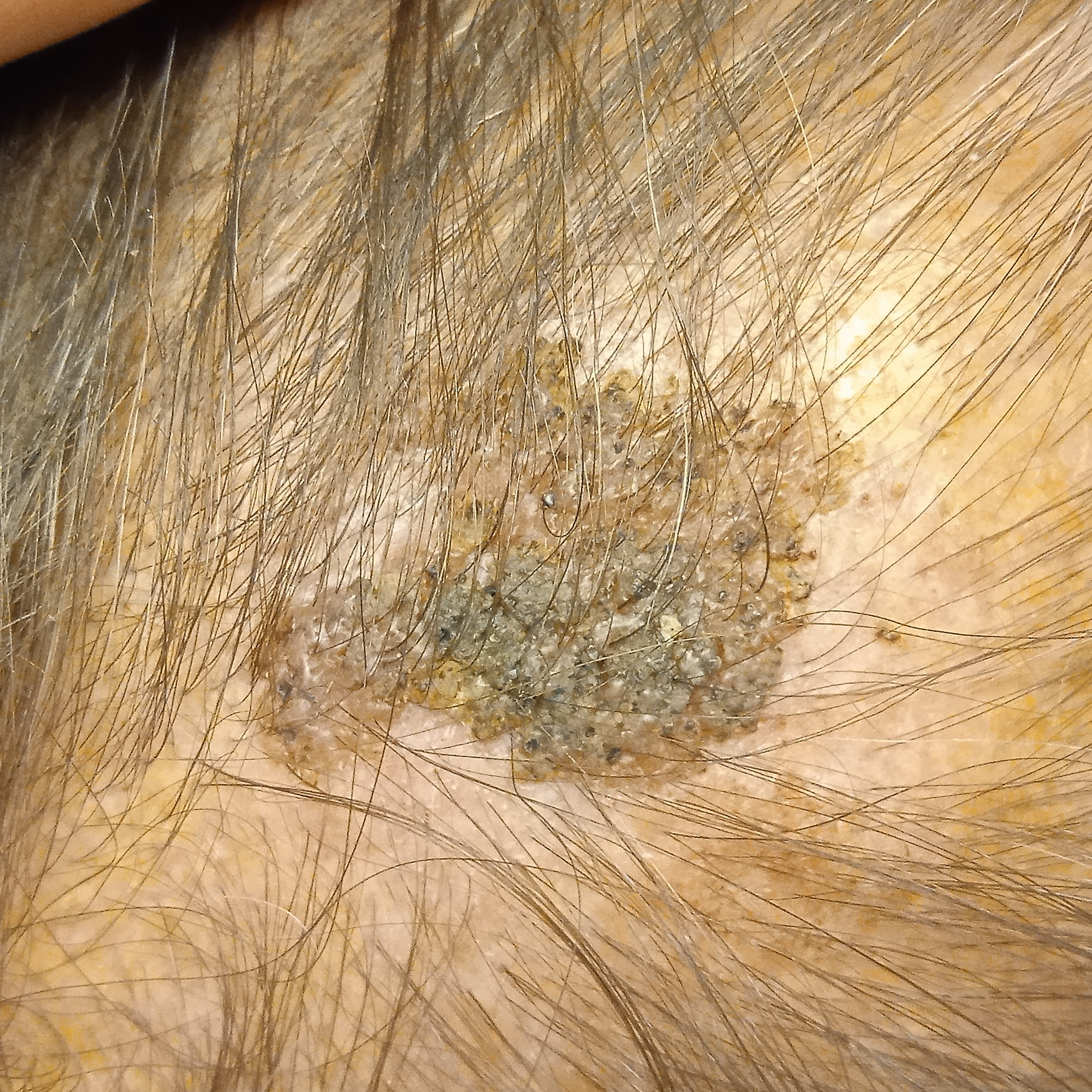Q: What is the referral context?
A: research study (no referral diagnosis)
Q: Patient demographics?
A: male, 72 years of age
Q: Where is the lesion?
A: the head
Q: Lesion size?
A: 19.2 mm
Q: What was the diagnosis?
A: seborrheic keratosis (dermatologist consensus)